Skin tone: Fitzpatrick phototype IV. The head or neck and arm are involved. The lesion is described as flat and raised or bumpy. Reported lesion symptoms include burning. The patient described the issue as a rash. Reported duration is less than one week. This is a close-up image.
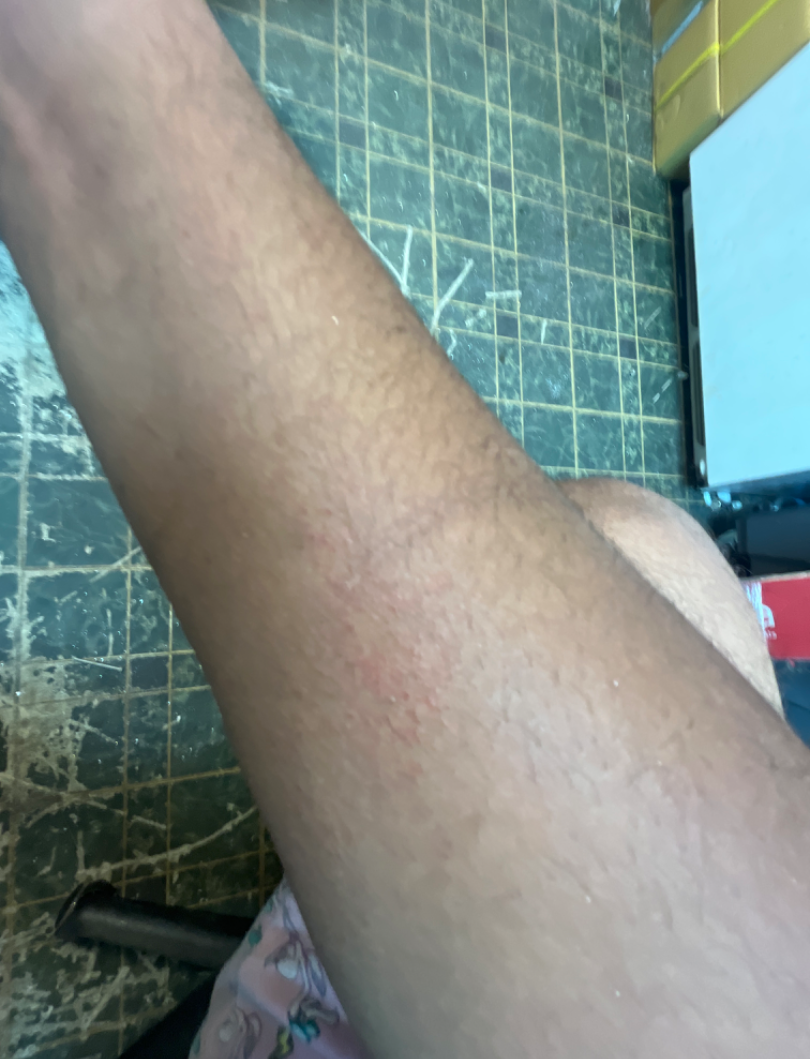assessment: Eczema (0.67); Allergic Contact Dermatitis (0.33).